The photograph was taken at an angle.
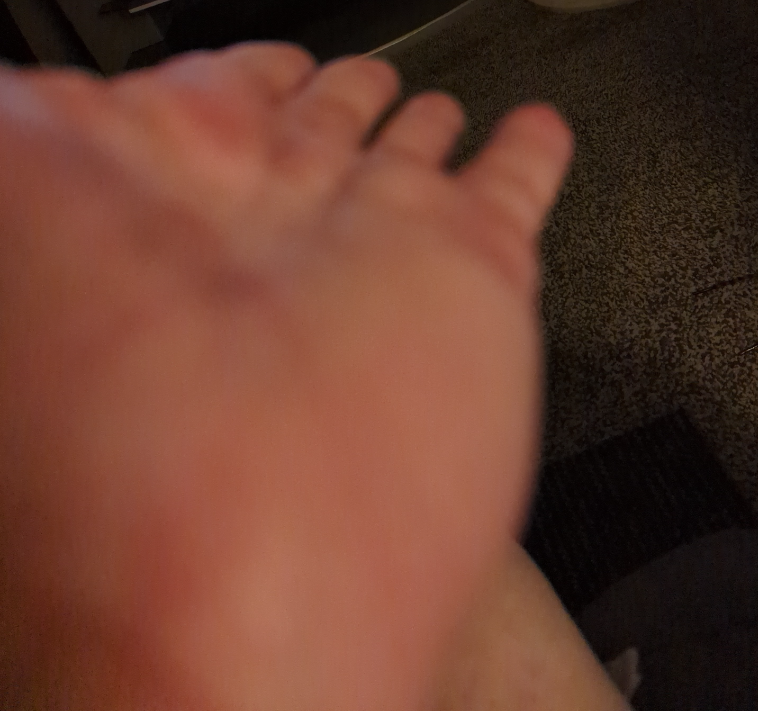{"differential": {"leading": ["Eczema"]}}